A dermoscopic image of a skin lesion.
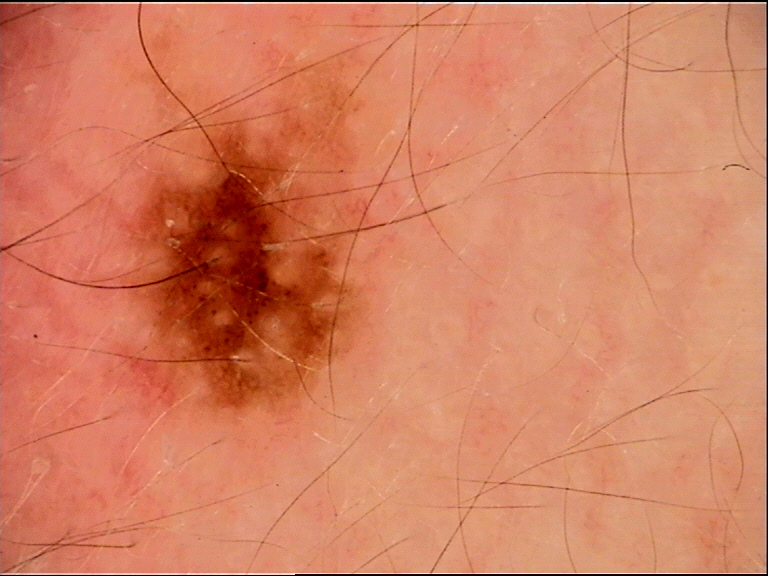{
  "diagnosis": {
    "name": "Miescher nevus",
    "code": "mcb",
    "malignancy": "benign",
    "super_class": "melanocytic",
    "confirmation": "expert consensus"
  }
}